Dermoscopy of a skin lesion.
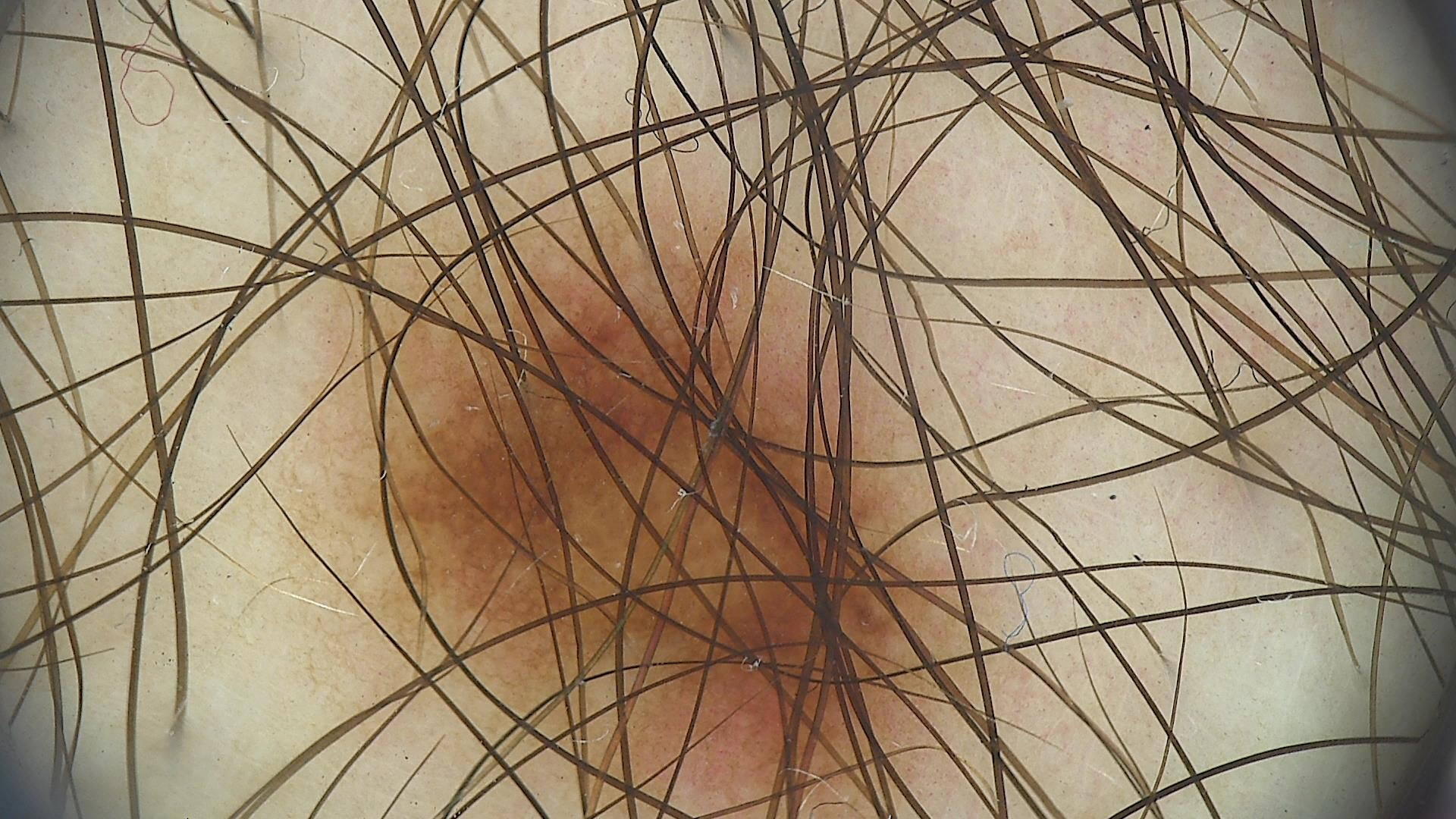The diagnosis was a dysplastic junctional nevus.